A smartphone photograph of a skin lesion · a subject in their early 30s: 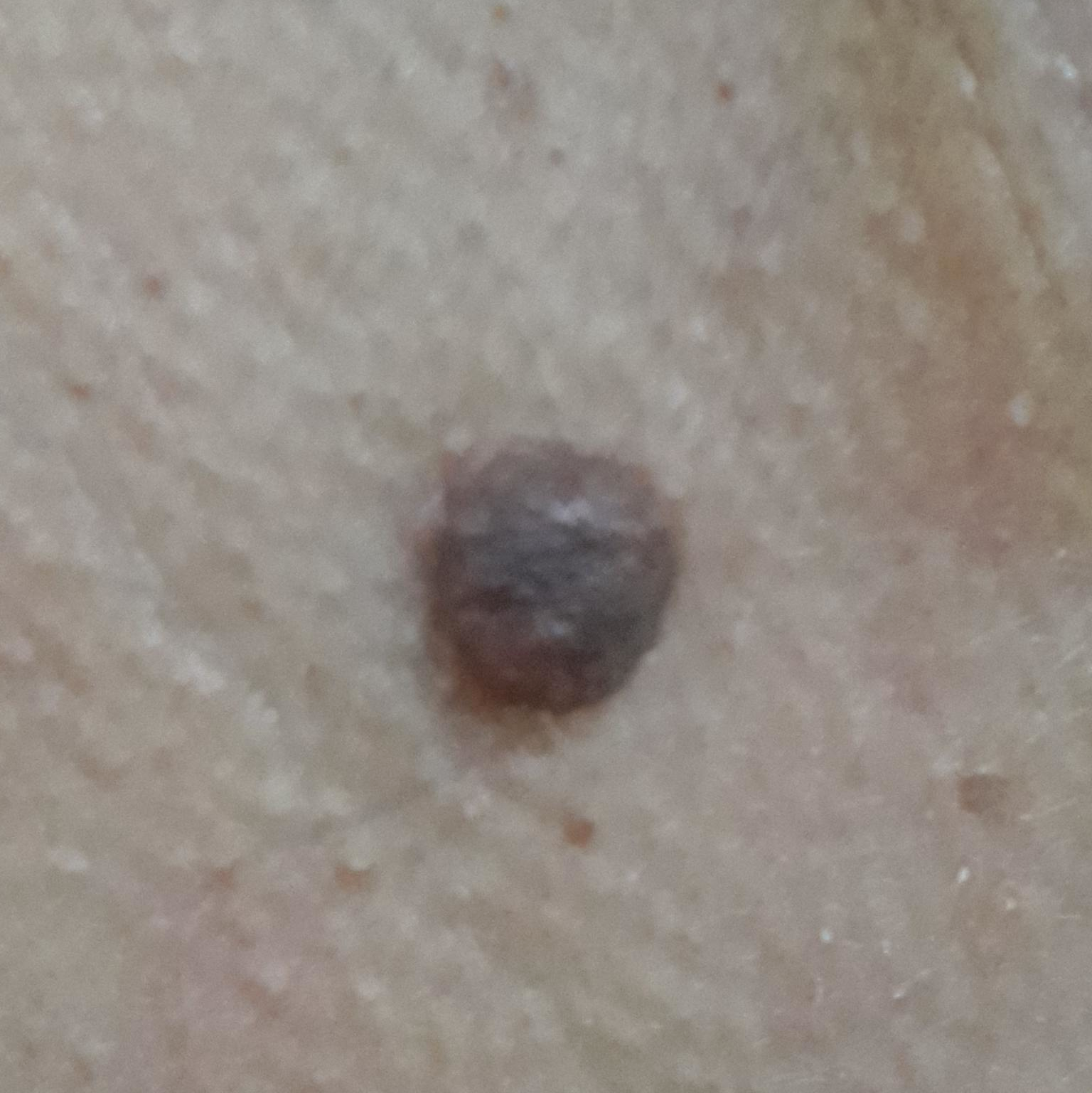The lesion is located on the neck.
The patient reports that the lesion is elevated and has grown.
Consistent with a nevus.